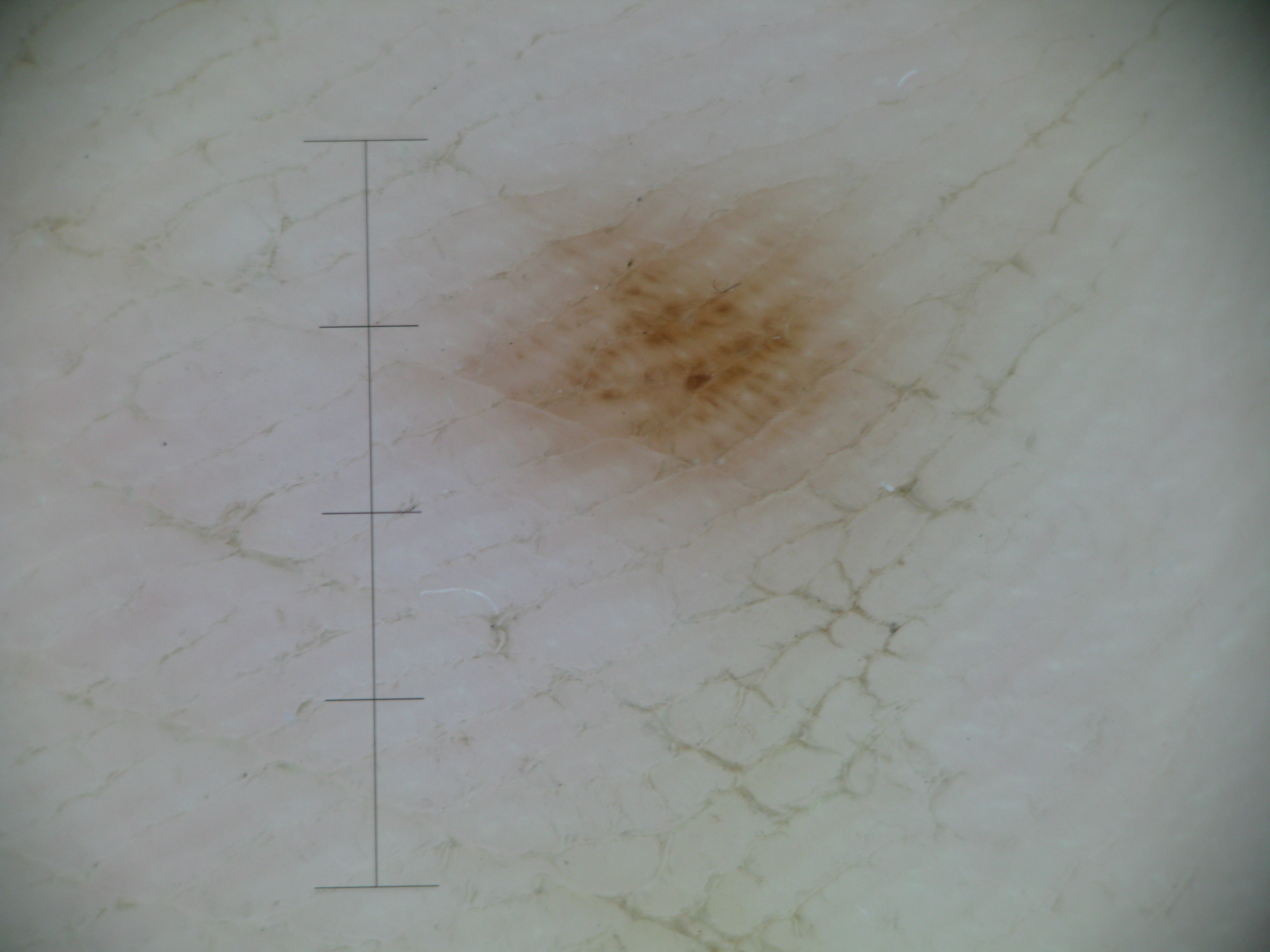Consistent with an acral junctional nevus.